The lesion involves the back of the hand, top or side of the foot and leg. The photograph is a close-up of the affected area. The lesion is described as raised or bumpy. Self-categorized by the patient as a rash: 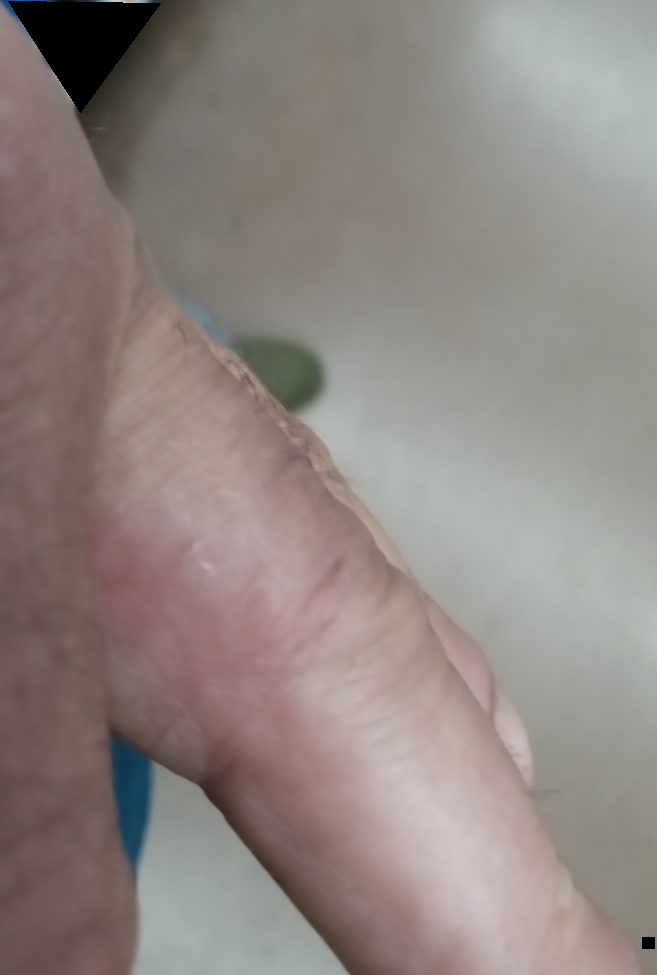assessment: ungradable on photographic review